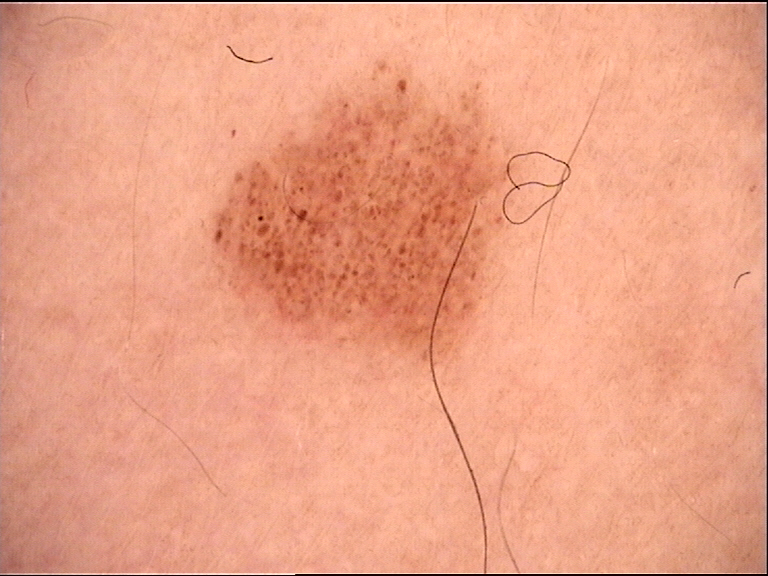Q: What kind of image is this?
A: dermoscopy
Q: What is the diagnosis?
A: dysplastic junctional nevus (expert consensus)